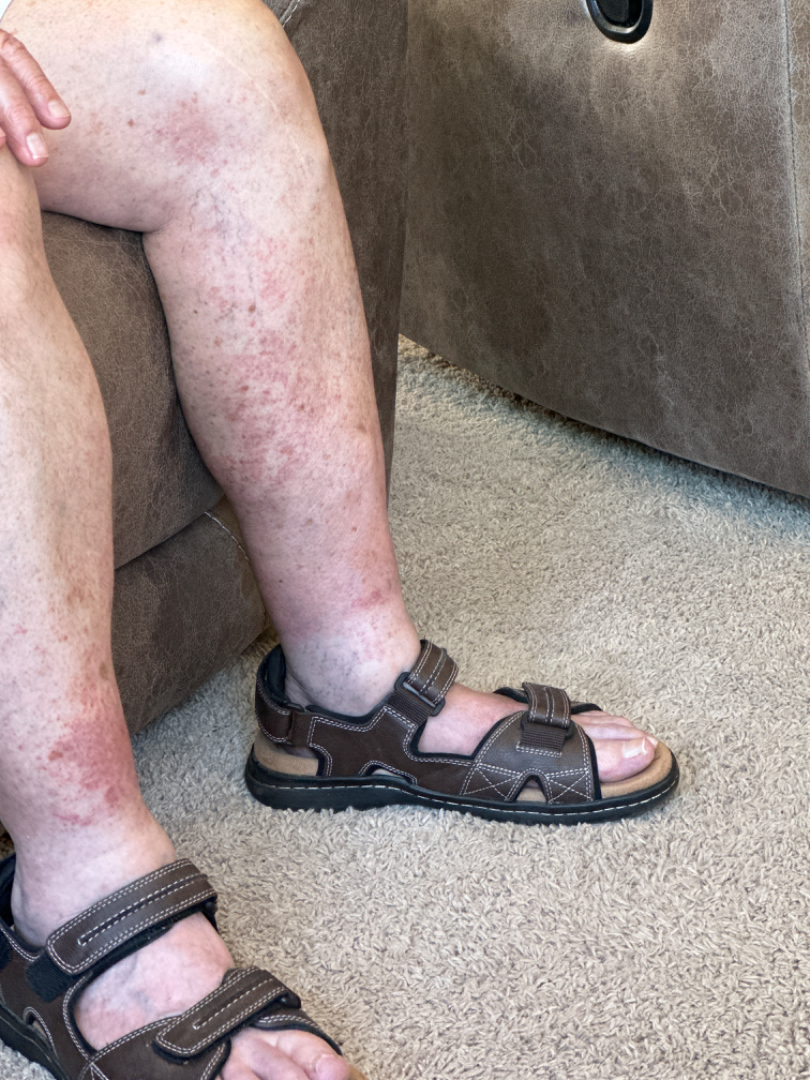reported symptoms: darkening, location: leg, patient's own categorization: a rash, lesion texture: flat, view: close-up, differential: the leading consideration is Leukocytoclastic Vasculitis; also consider Pigmented purpuric eruption; less likely is Stasis Dermatitis.